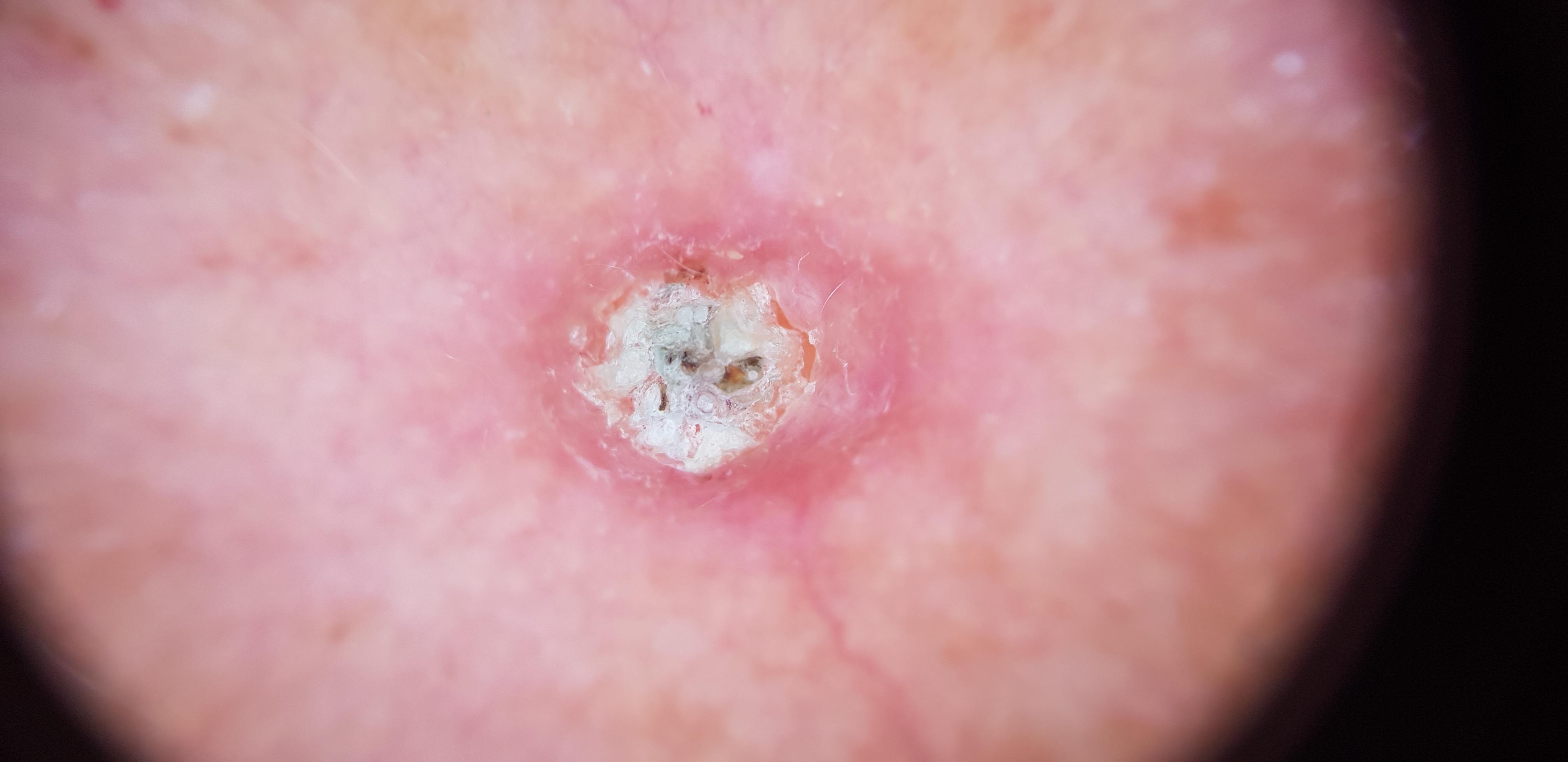skin phototype=II | patient=female, in their mid-70s | pathology=Solar or actinic keratosis (biopsy-proven).